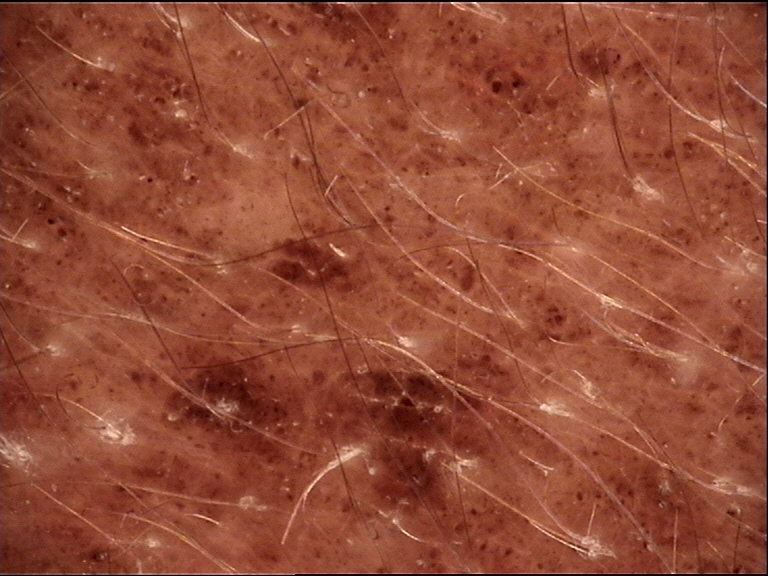<dermoscopy>
  <image>dermatoscopy</image>
  <diagnosis>
    <name>congenital compound nevus</name>
    <code>ccb</code>
    <malignancy>benign</malignancy>
    <super_class>melanocytic</super_class>
    <confirmation>expert consensus</confirmation>
  </diagnosis>
</dermoscopy>